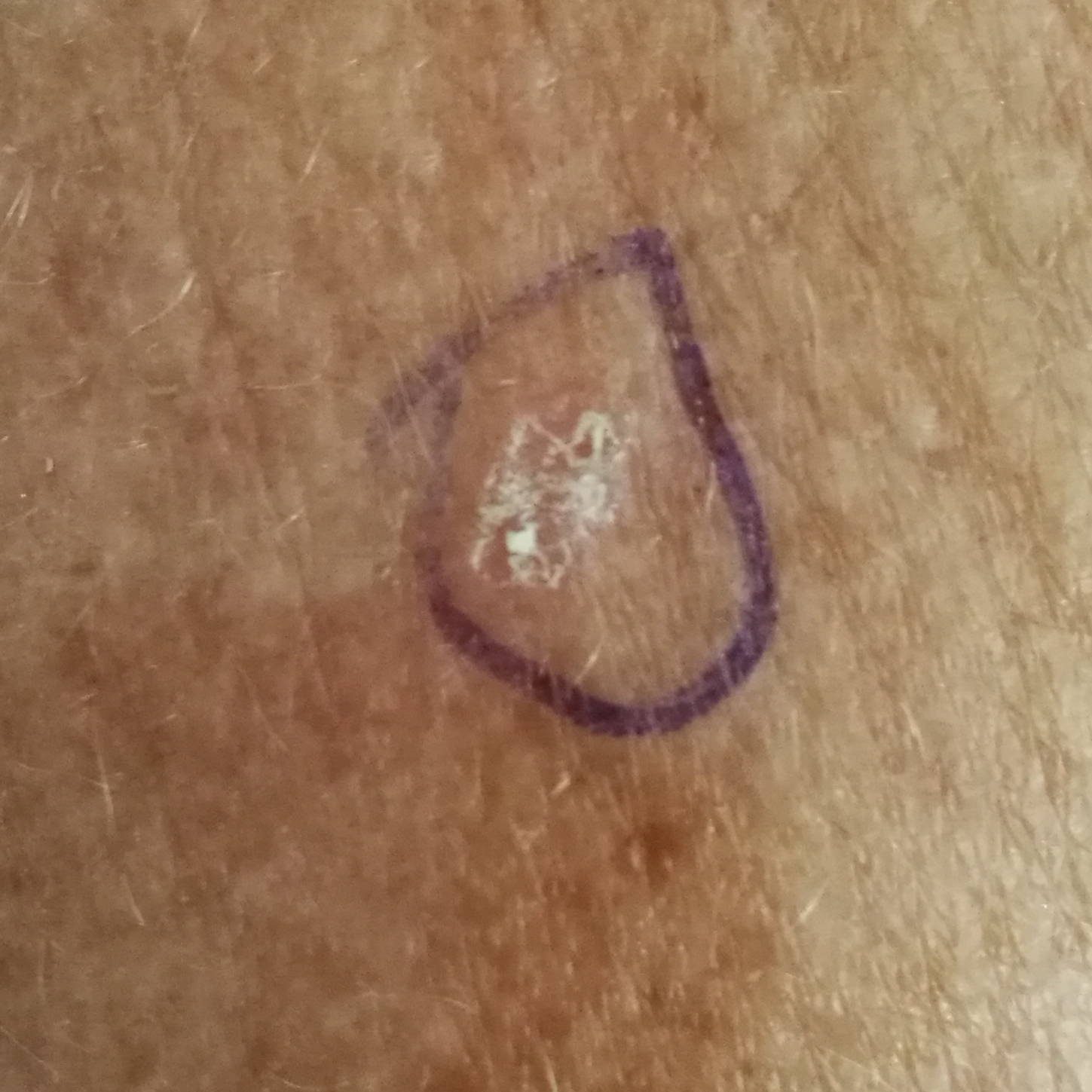Q: What is the imaging modality?
A: clinical photograph
Q: Who is the patient?
A: 58 years old
Q: What is the anatomic site?
A: a forearm
Q: What is this lesion?
A: actinic keratosis (clinical consensus)